The patient considered this a rash. The contributor reports the condition has been present for one to four weeks. This is a close-up image. Symptoms reported: itching and enlargement. The lesion involves the arm.
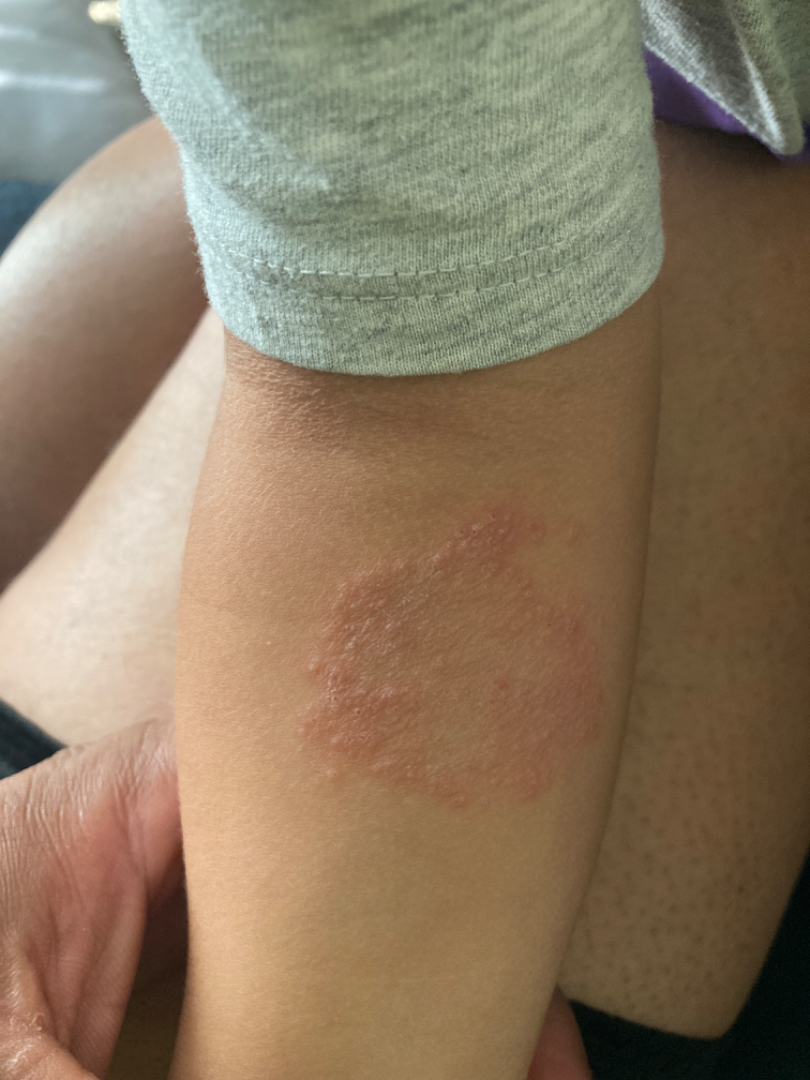differential = a single dermatologist reviewed the case: most consistent with Psoriasis; with consideration of Tinea; also consider Eczema.